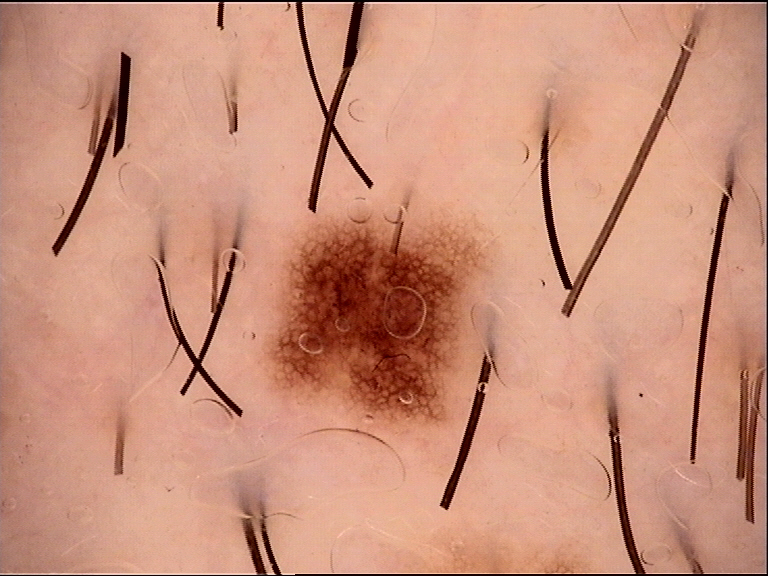Q: What is the imaging modality?
A: dermoscopy
Q: What is this lesion?
A: dysplastic junctional nevus (expert consensus)